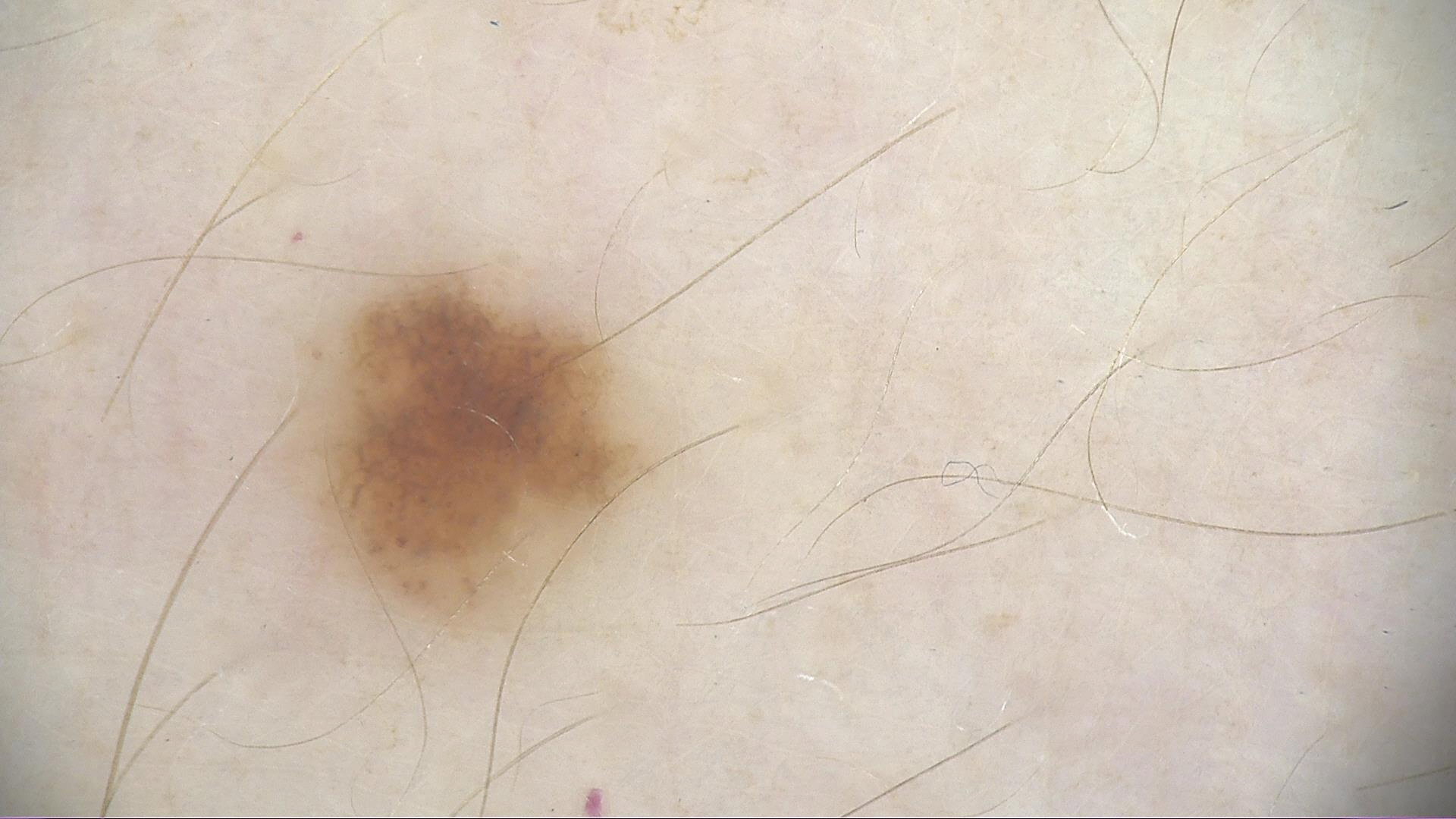A dermoscopy image of a single skin lesion.
Diagnosed as a dysplastic junctional nevus.